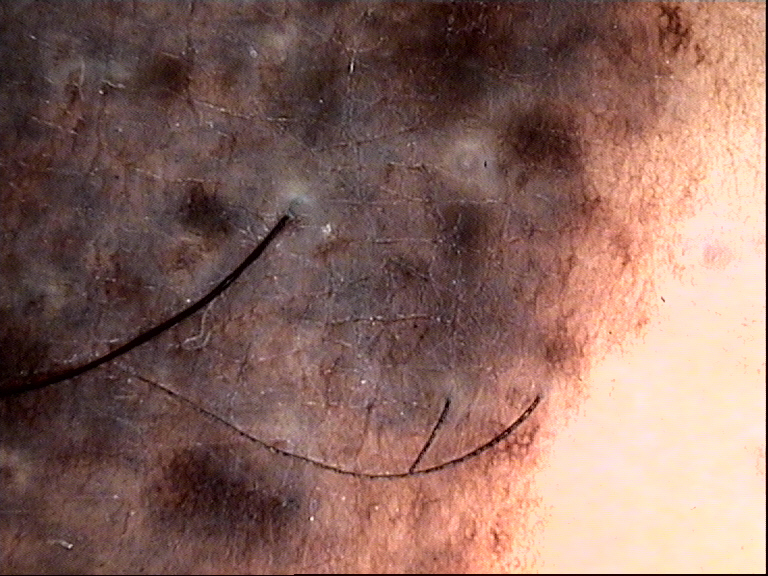Consistent with a congenital compound nevus.